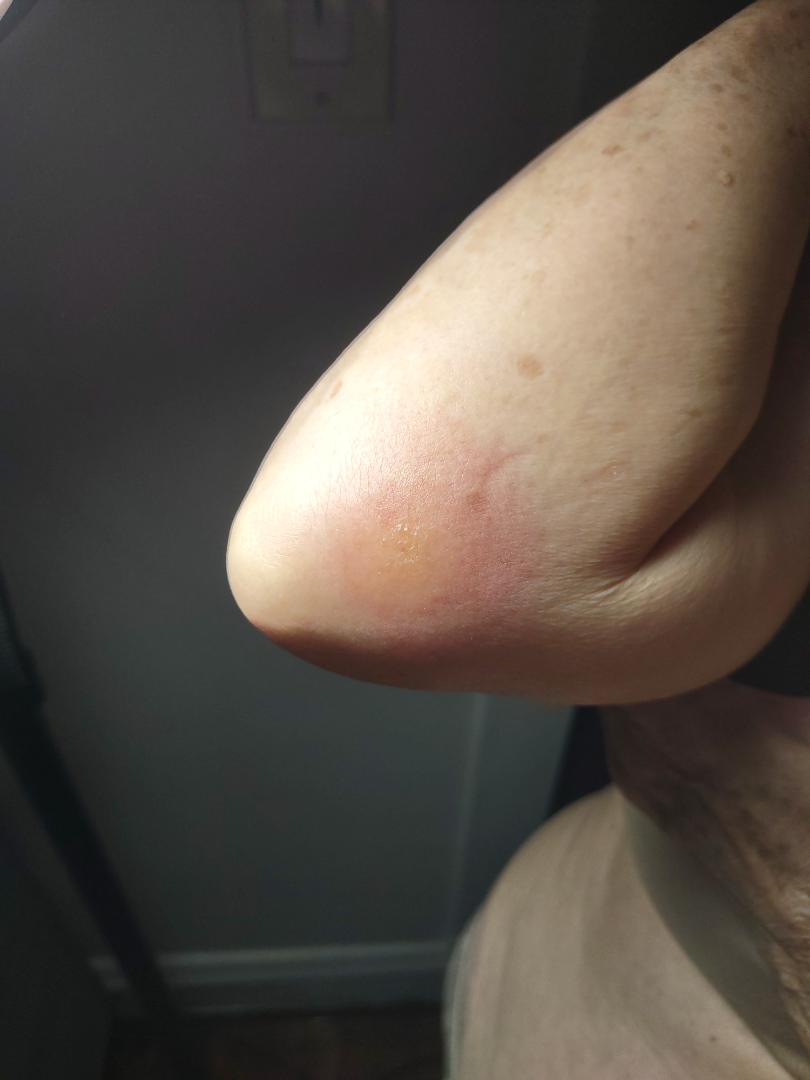The reviewer was unable to grade this case for skin condition.